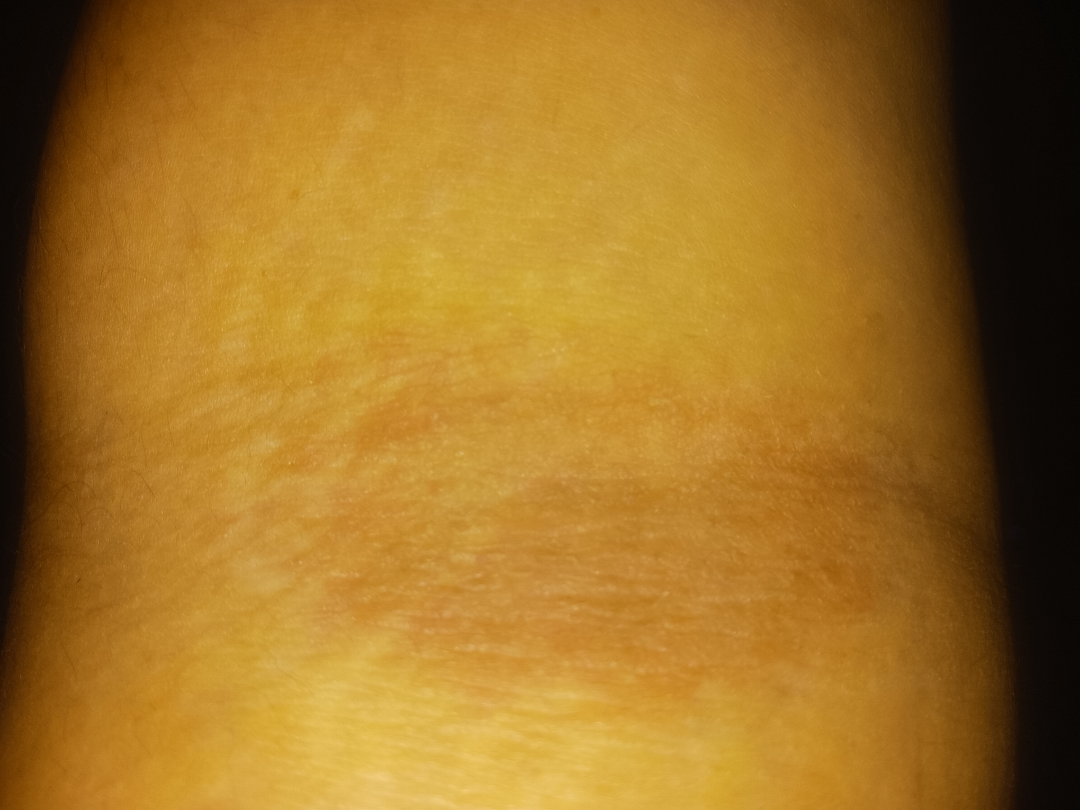The dermatologist could not determine a likely condition from the photograph alone.
The patient reports the lesion is rough or flaky.
Self-categorized by the patient as a rash.
The arm is involved.
Present for one to four weeks.
The patient is 40–49, female.
A close-up photograph.
Symptoms reported: enlargement, burning, darkening and itching.
No constitutional symptoms were reported.